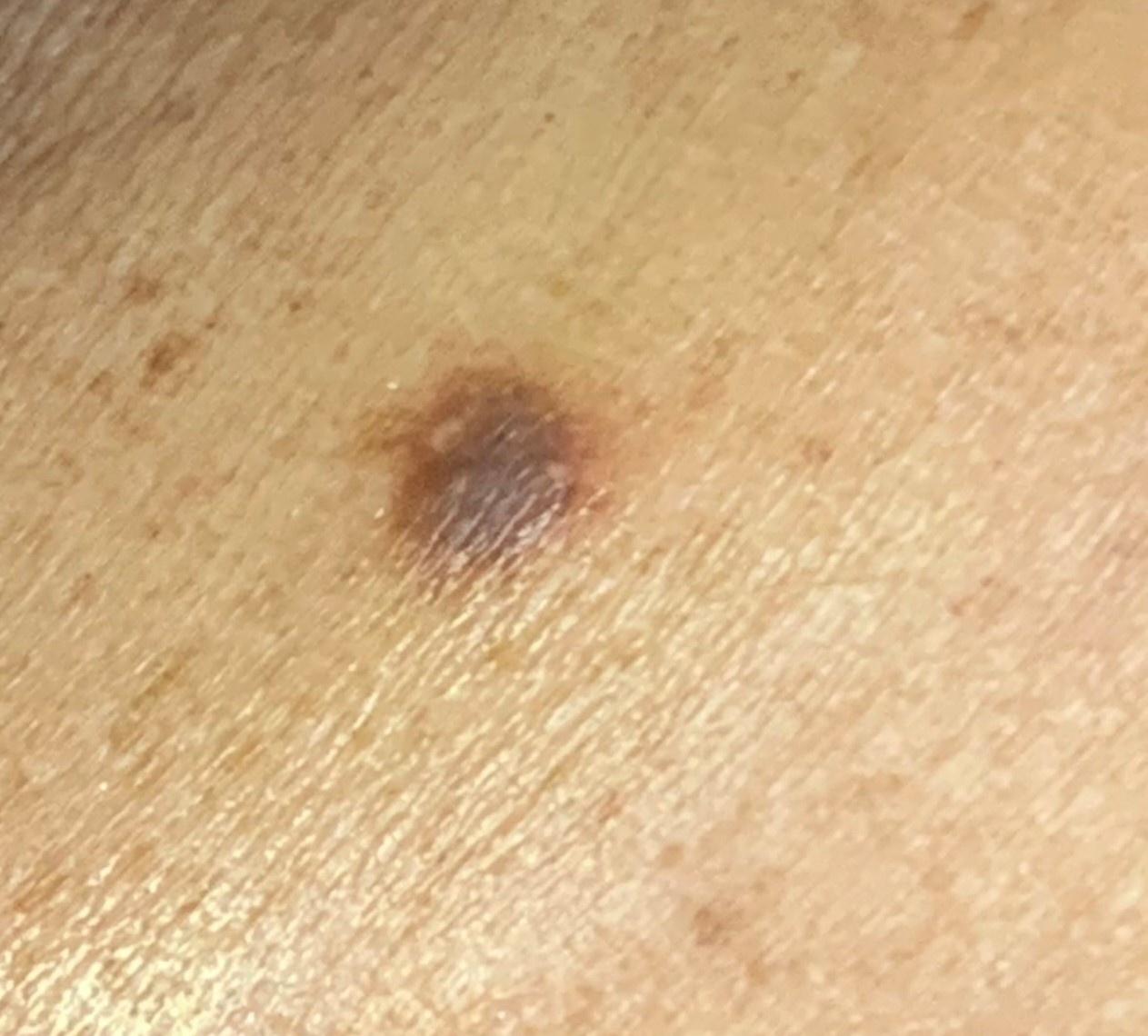A wide-field clinical photograph of a skin lesion. A female subject roughly 45 years of age. Located on an upper extremity. On biopsy, the diagnosis was a dermatofibroma.